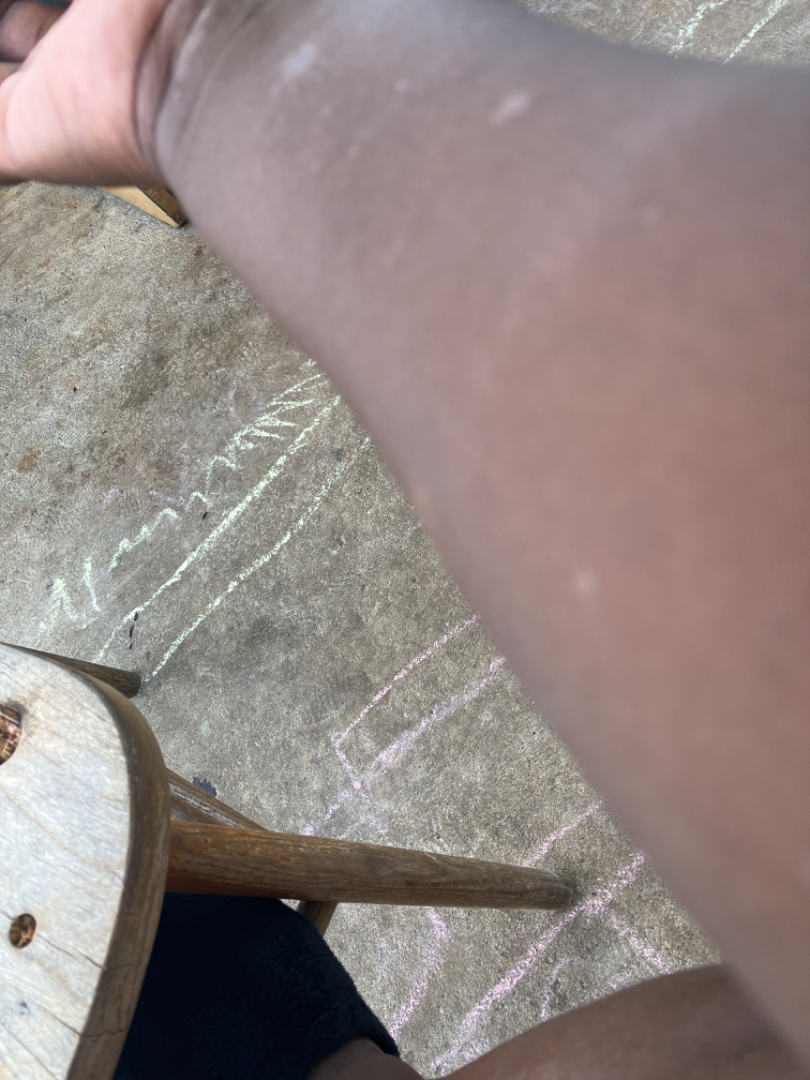clinical impression: the differential includes Chronic dermatitis, NOS and Allergic Contact Dermatitis, with no clear leading consideration